The photograph is a close-up of the affected area — 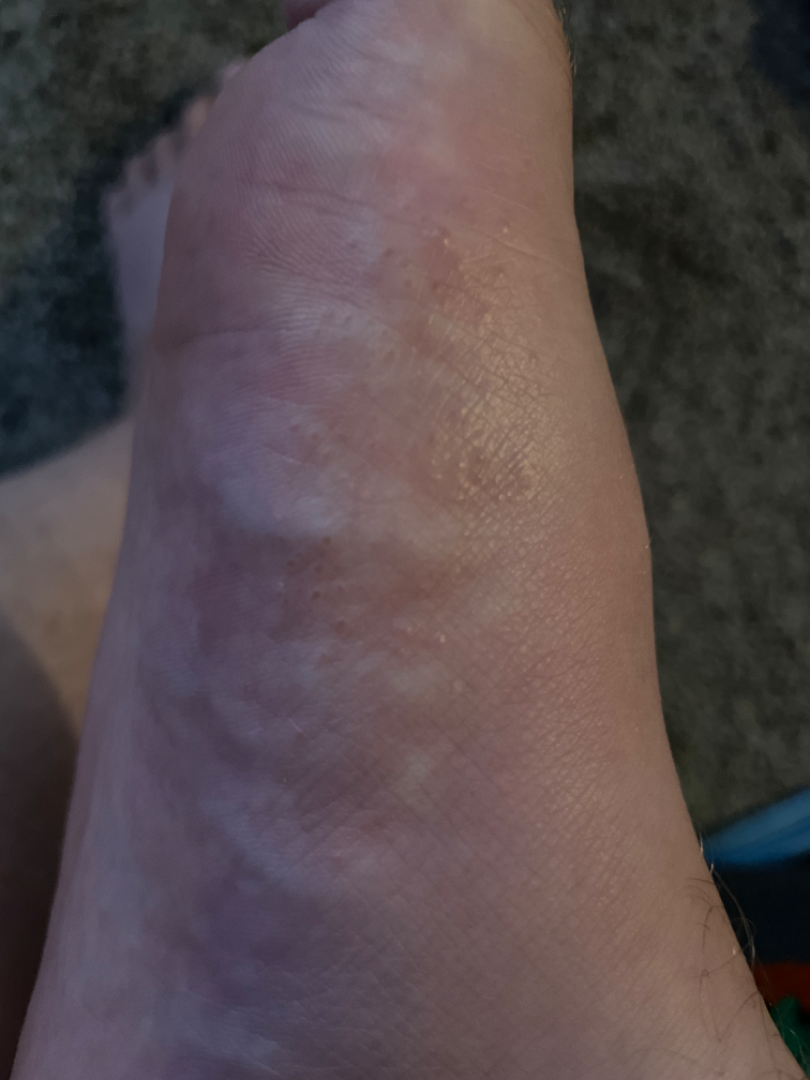assessment: unable to determine.